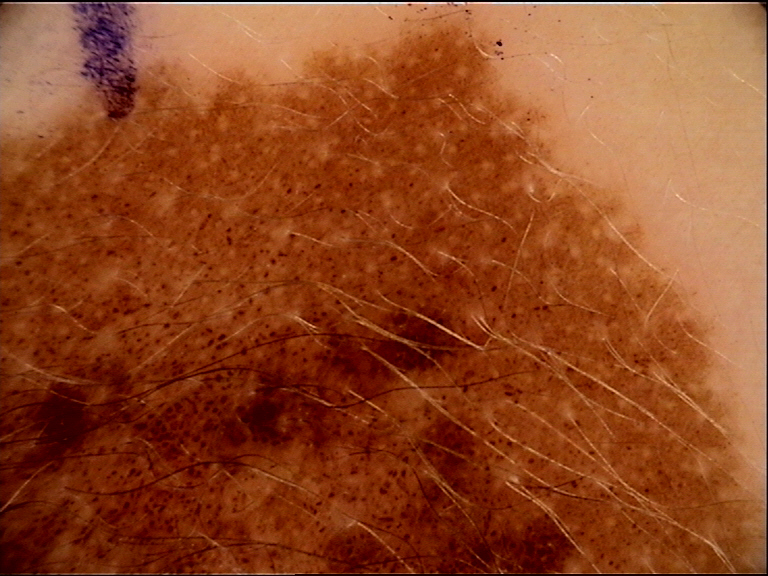Dermoscopy of a skin lesion. The diagnosis was a congenital junctional nevus.